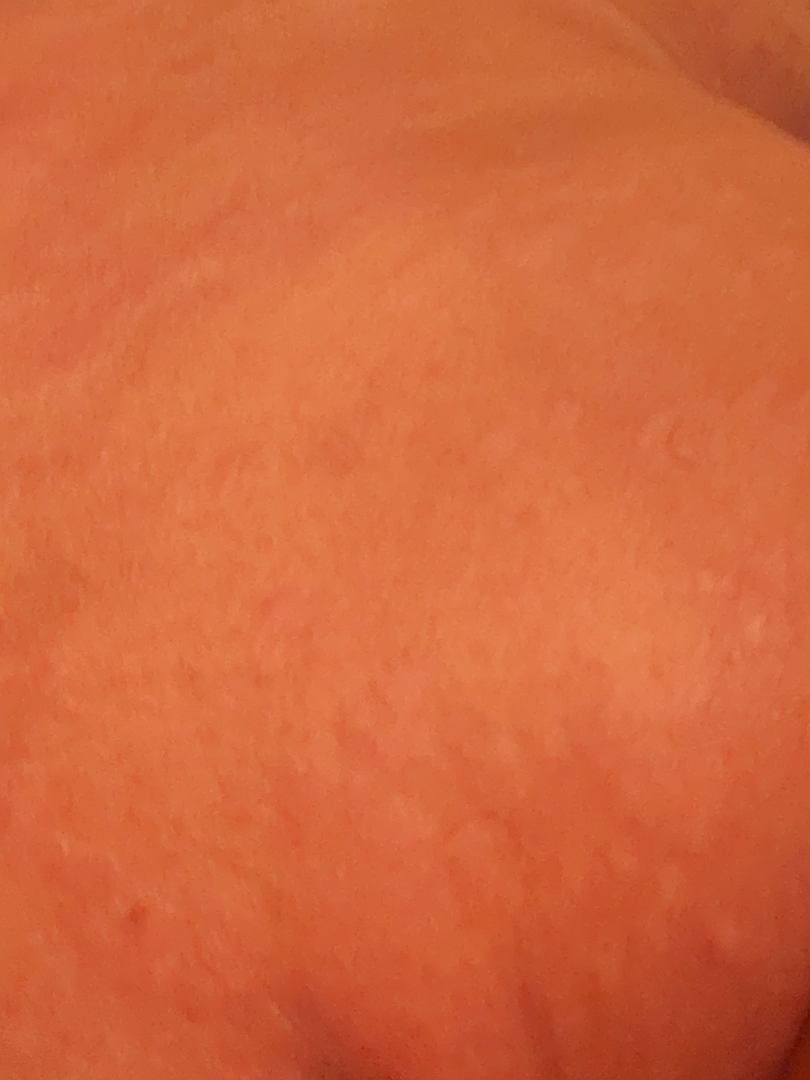{
  "assessment": "not assessable",
  "patient_category": "a rash",
  "duration": "less than one week",
  "body_site": [
    "head or neck",
    "arm"
  ],
  "shot_type": "at an angle",
  "texture": "raised or bumpy",
  "symptoms": [
    "enlargement",
    "itching",
    "bothersome appearance"
  ]
}